Acquired for a research image collection, with no referral diagnosis · the patient says their skin tans without first burning · a dermoscopy image of a skin lesion · a male patient 79 years old · the patient describes having few moles overall — 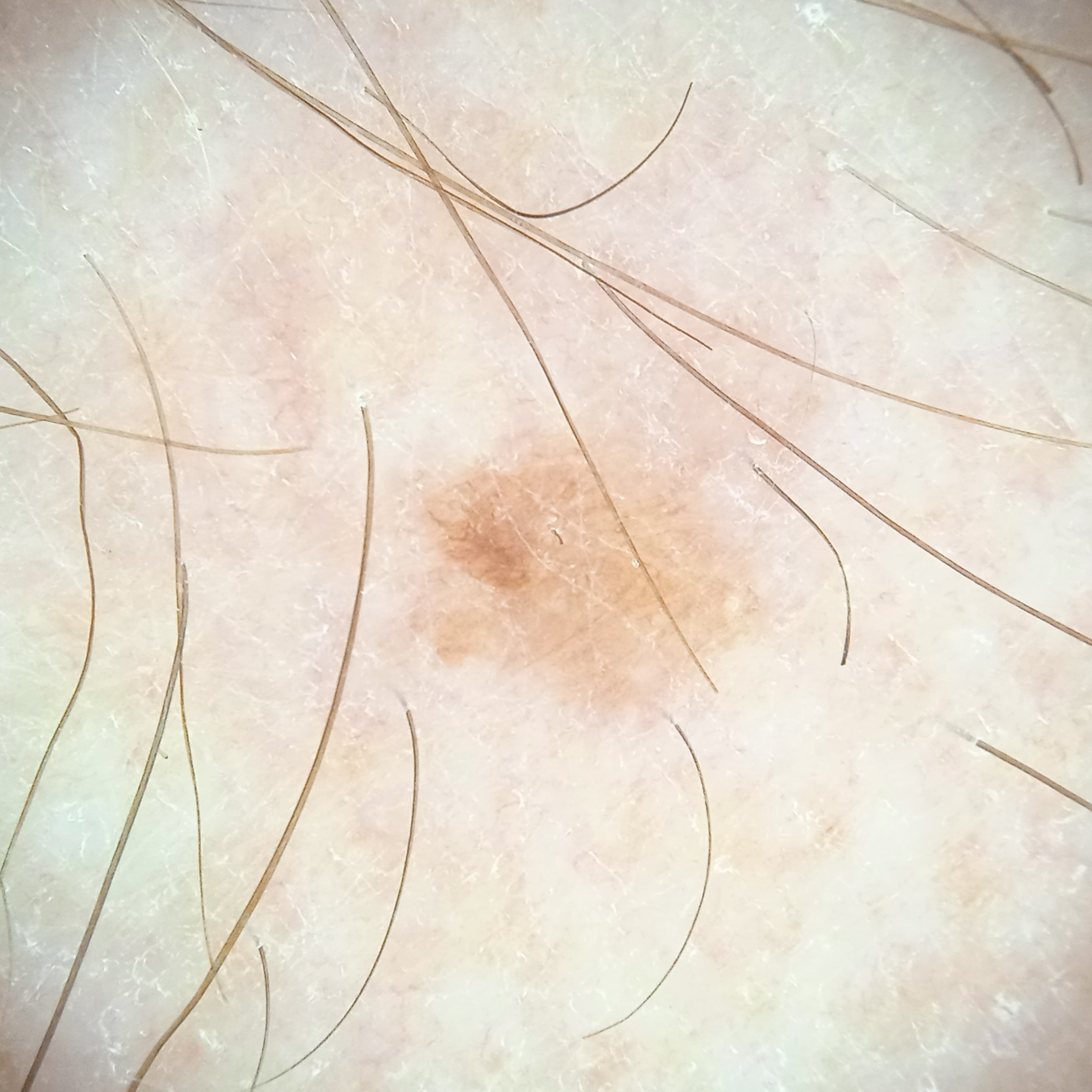Clinical context:
The lesion measures approximately 4.2 mm.
Conclusion:
The lesion was assessed as a seborrheic keratosis.